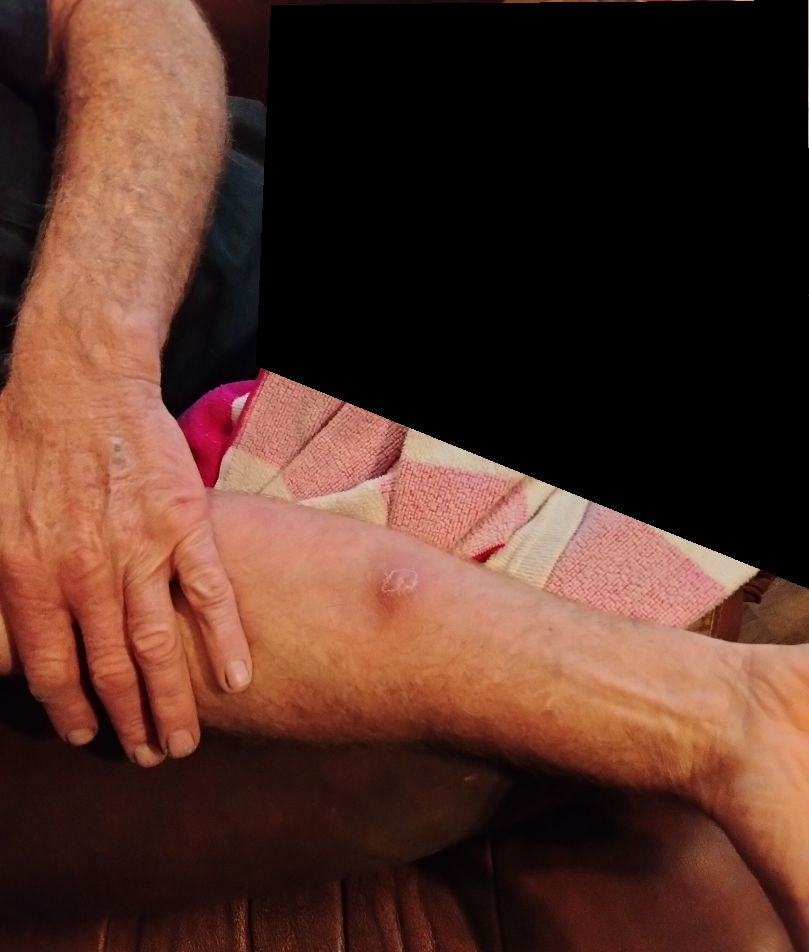The arm is involved. The photo was captured at a distance. The subject is male. One reviewing dermatologist: most consistent with pustules.